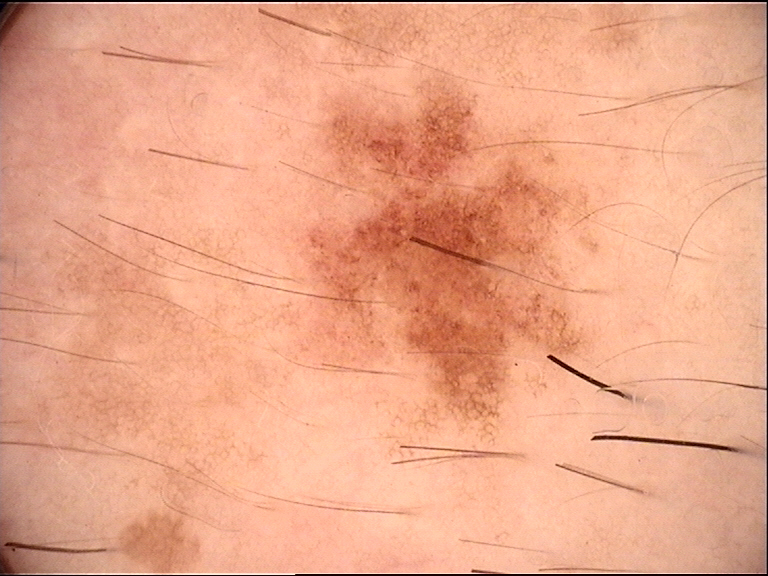{"diagnosis": {"name": "dysplastic junctional nevus", "code": "jd", "malignancy": "benign", "super_class": "melanocytic", "confirmation": "expert consensus"}}